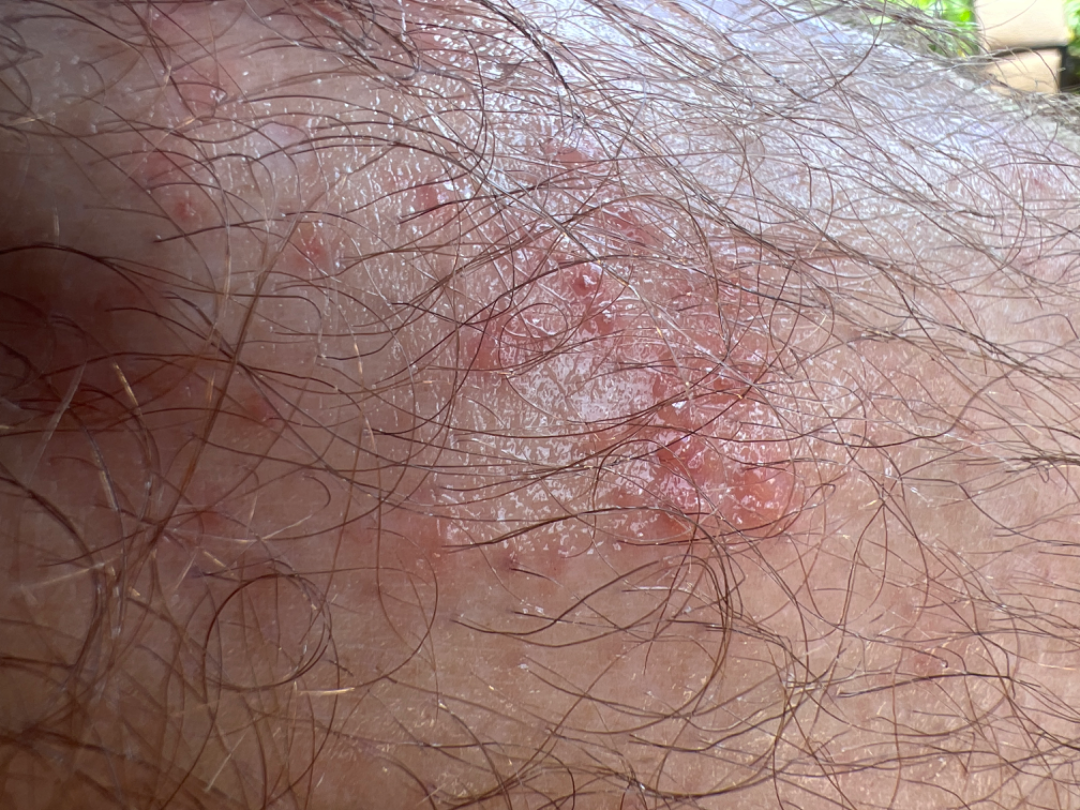| feature | finding |
|---|---|
| assessment | indeterminate |
| onset | less than one week |
| body site | leg |
| lesion symptoms | enlargement |
| described texture | fluid-filled and raised or bumpy |
| patient | male, age 50–59 |
| shot type | at an angle |
| patient's own categorization | a rash |